Dermoscopy of a skin lesion · the patient is a male aged around 35:
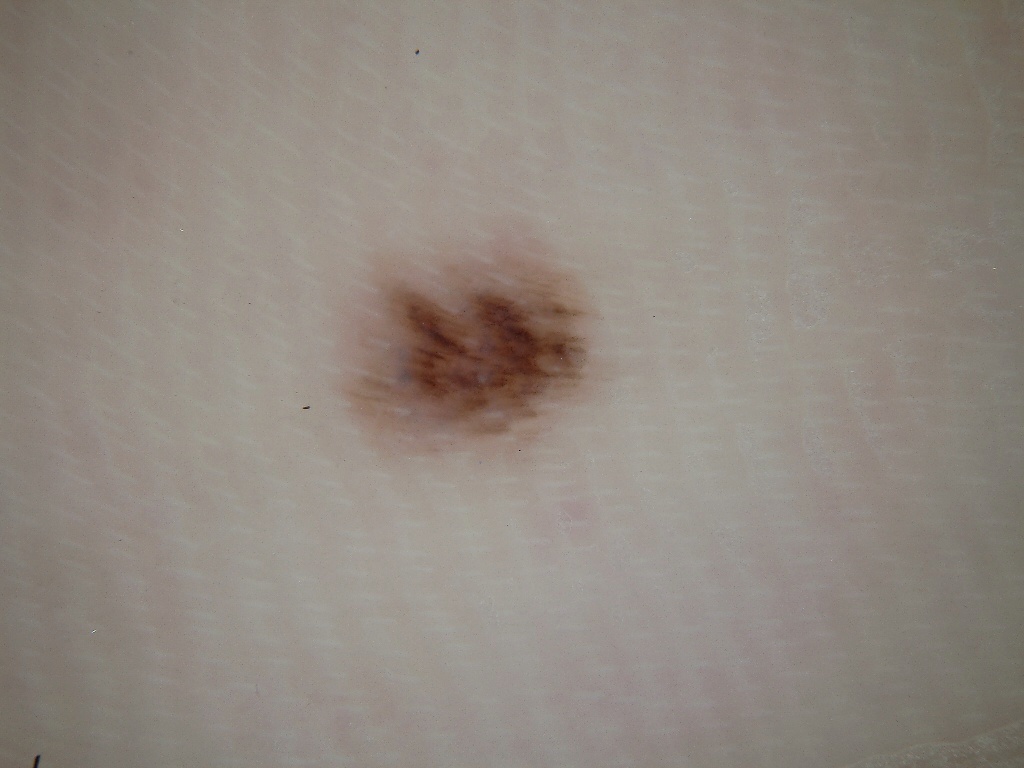Q: What is the lesion's bounding box?
A: bbox=[303, 206, 631, 476]
Q: Which assessed dermoscopic features were absent?
A: milia-like cysts, streaks, pigment network, negative network, and globules
Q: How much of the field does the lesion occupy?
A: ~9% of the field
Q: What is this lesion?
A: a melanocytic nevus, a benign lesion